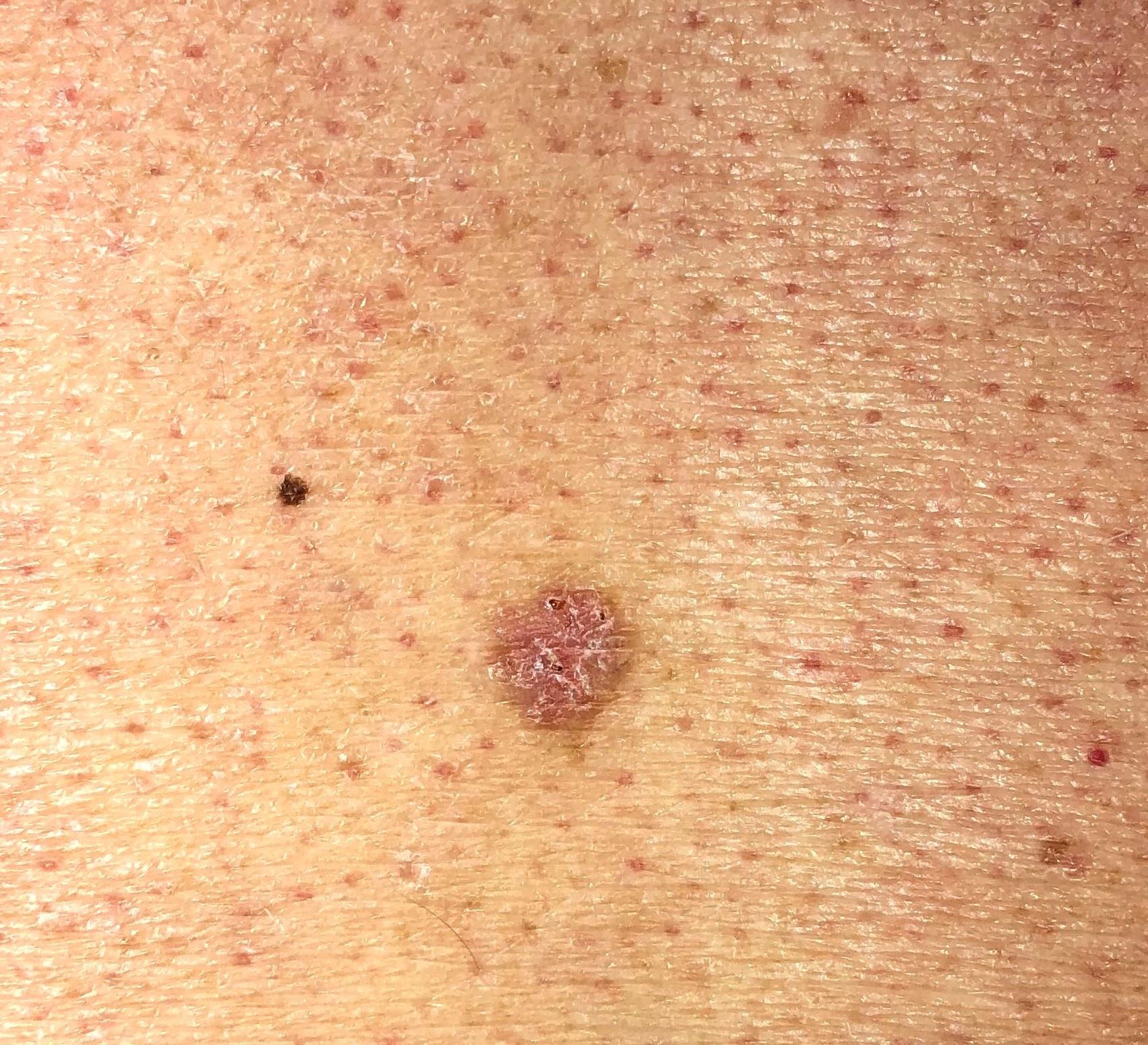Skin type II. A male patient aged 63 to 67. A clinical photograph showing a skin lesion in context. The chart records no first-degree relative with melanoma and no previous melanoma. On biopsy, the diagnosis was a basal cell carcinoma.